No associated systemic symptoms reported; reported duration is more than five years; texture is reported as flat; the patient is a male aged 40–49; no relevant lesion symptoms reported; close-up view; the patient considered this skin that appeared healthy to them; the affected area is the leg, front of the torso and arm:
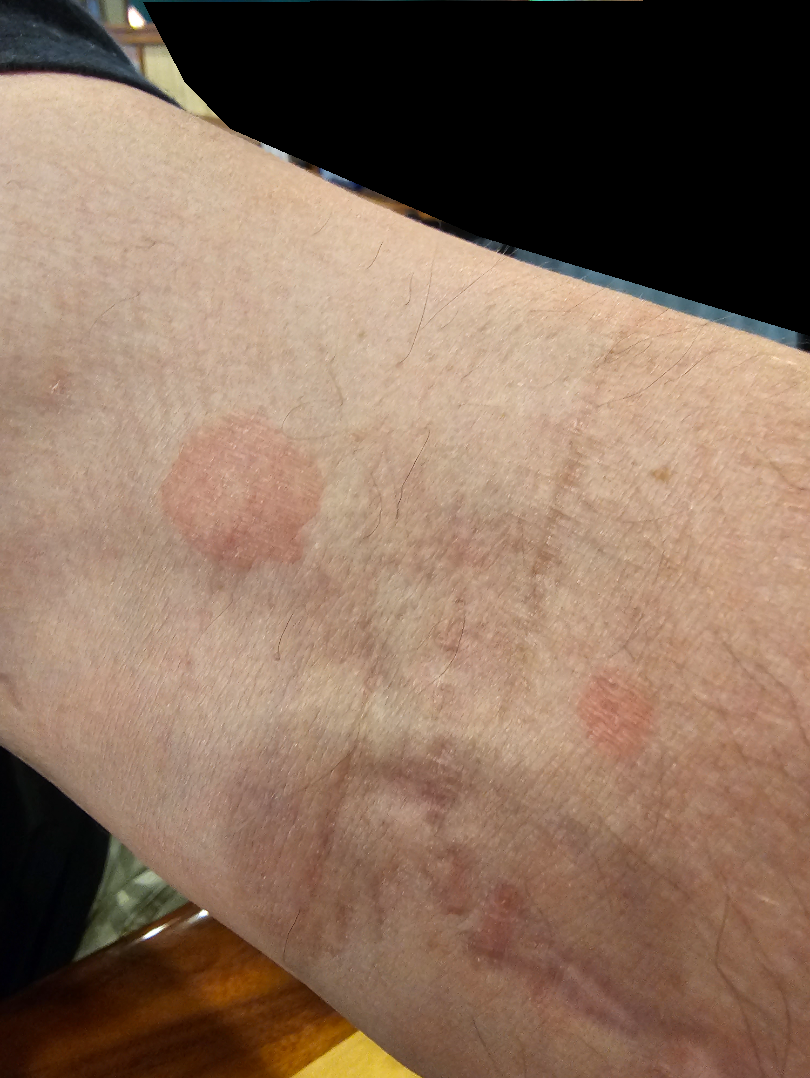<summary>
<differential>
  <Tinea Versicolor>0.43</Tinea Versicolor>
  <Psoriasis>0.22</Psoriasis>
  <Tinea>0.13</Tinea>
  <Eczema>0.13</Eczema>
  <Pityriasis rosea>0.09</Pityriasis rosea>
</differential>
</summary>